A dermatoscopic image of a skin lesion.
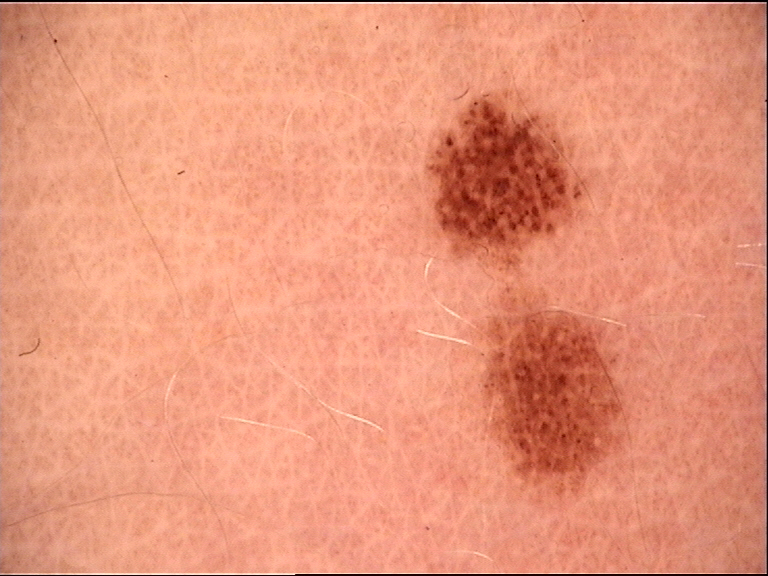diagnosis:
  name: dysplastic junctional nevus
  code: jd
  malignancy: benign
  super_class: melanocytic
  confirmation: expert consensus